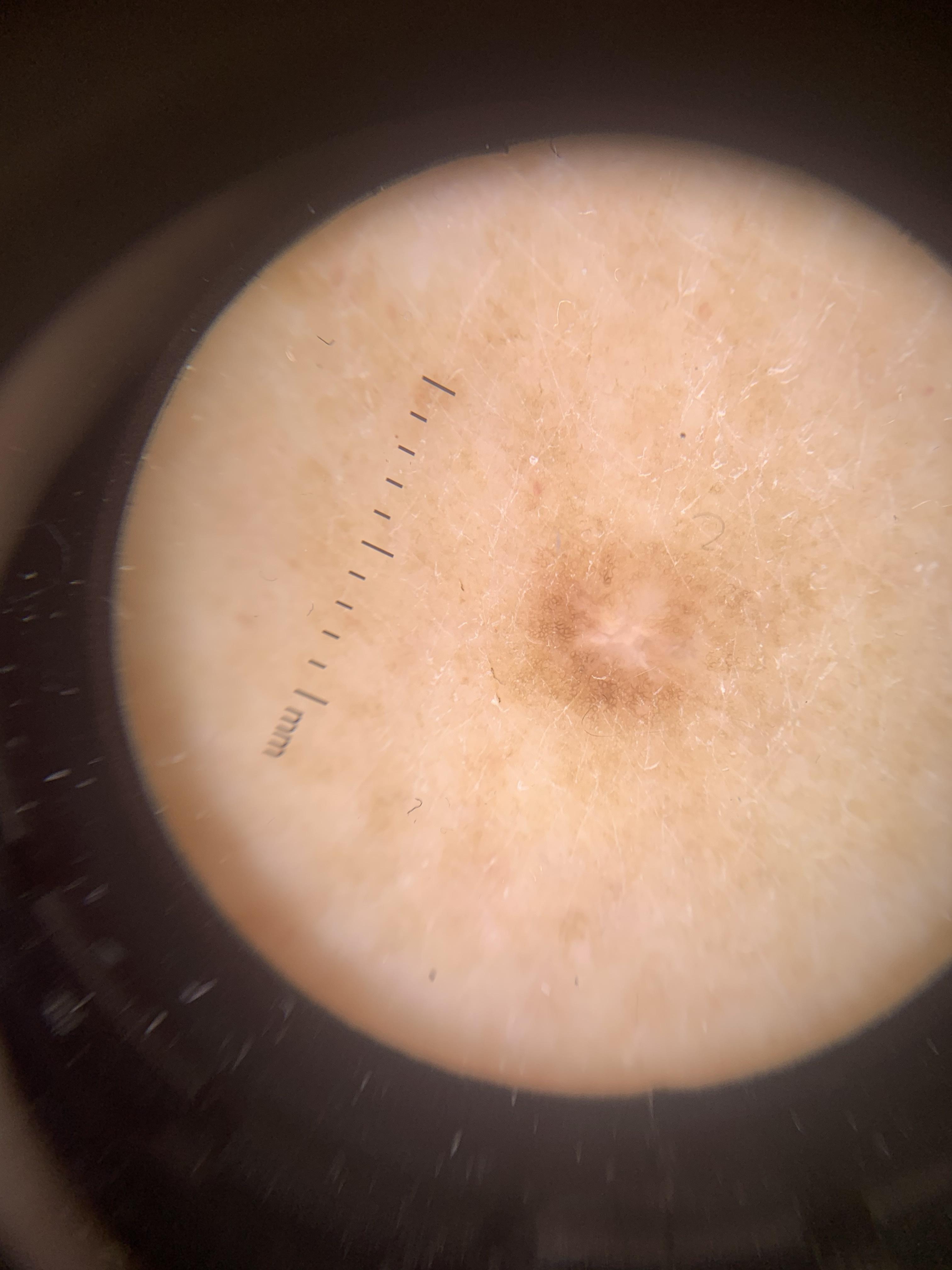site: a lower extremity; impression: Dermatofibroma.